The contributor is 40–49, male · the lesion involves the head or neck, back of the torso, arm, back of the hand and front of the torso · an image taken at an angle — 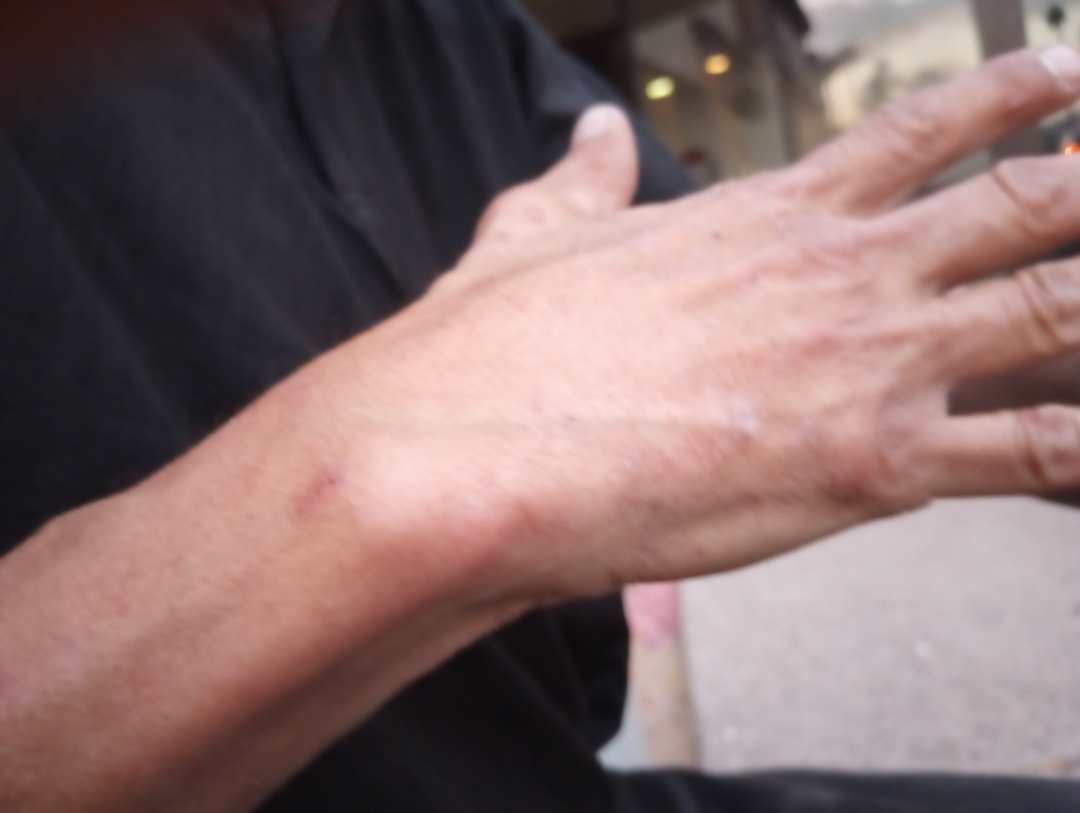<summary>
  <assessment>ungradable on photographic review</assessment>
</summary>